Skin tone: lay reviewers estimated a Monk Skin Tone of 3; the patient is 50–59, male; this image was taken at an angle.
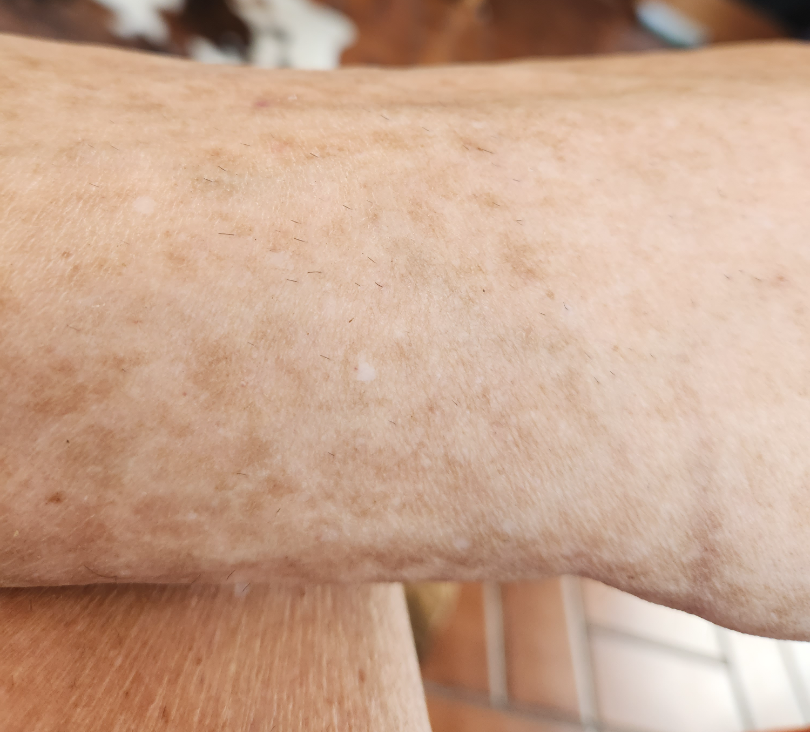Q: What is the dermatologist's impression?
A: in keeping with Pigmented purpuric eruption